No relevant systemic symptoms · self-categorized by the patient as acne · the lesion involves the front of the torso · skin tone: Fitzpatrick phototype II; lay graders estimated Monk Skin Tone 3 · symptoms reported: burning and bothersome appearance · the condition has been present for less than one week · male subject, age 40–49 · texture is reported as rough or flaky, raised or bumpy and fluid-filled · a close-up photograph: 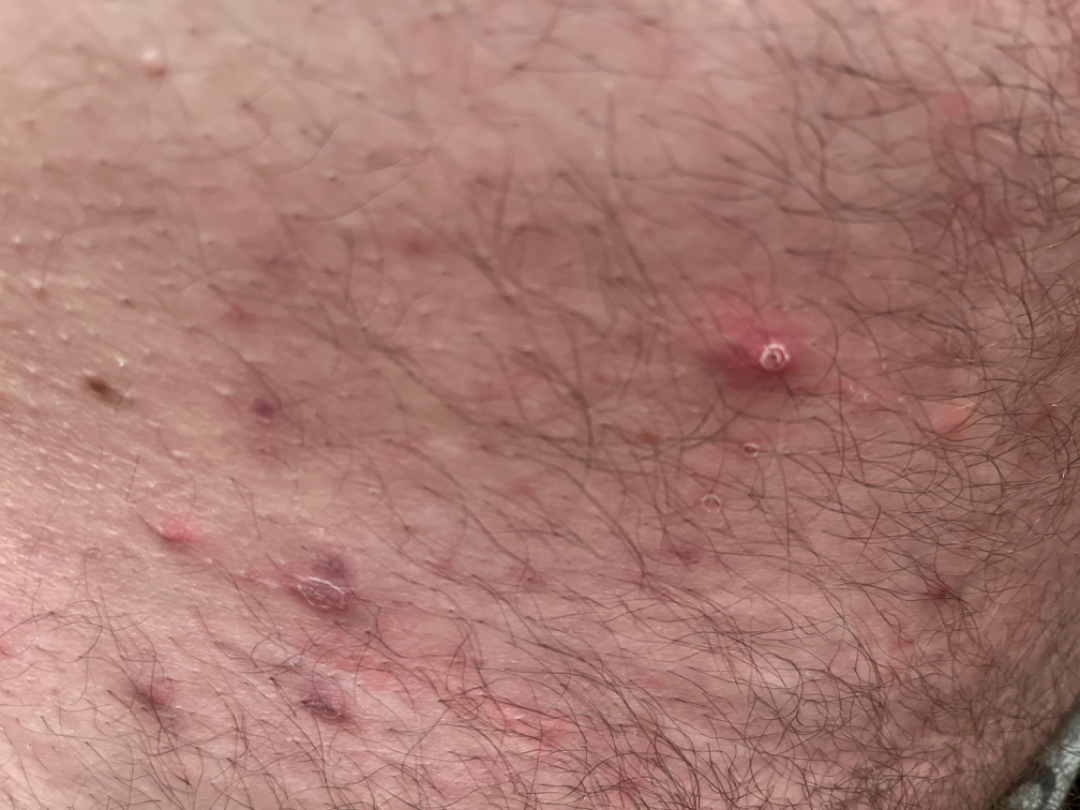assessment = the impression on review was Folliculitis.